A dermoscopic image of a skin lesion:
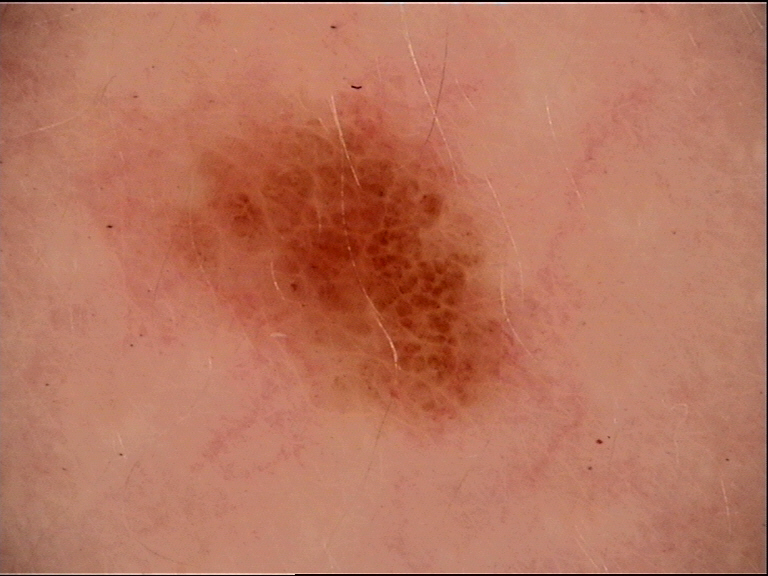Conclusion:
Labeled as a dysplastic junctional nevus.